Dermoscopy of a skin lesion.
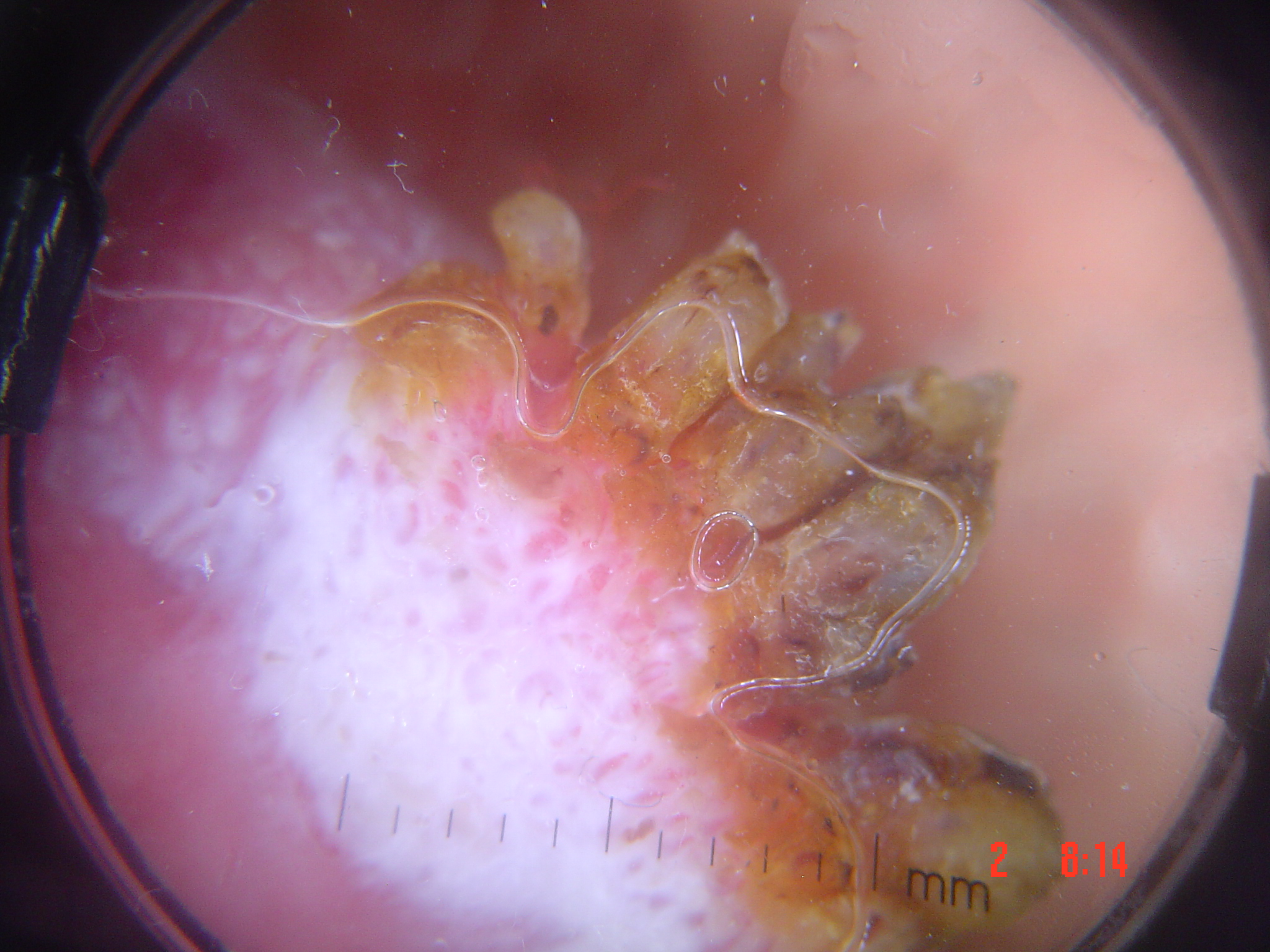Histopathology confirmed a malignant, keratinocytic lesion — a squamous cell carcinoma.